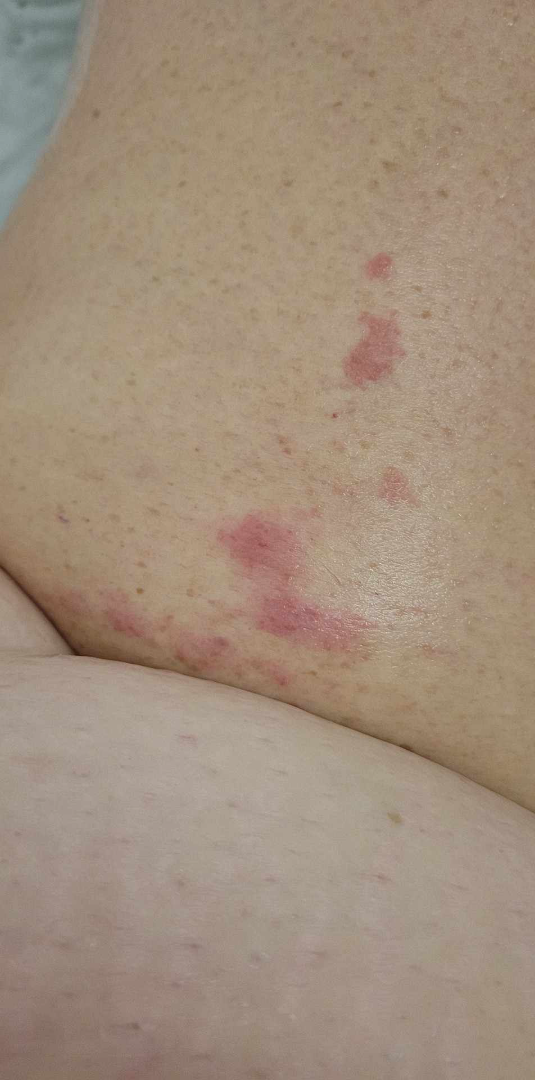assessment = unable to determine.